Collected as part of a research study, without a referral diagnosis; a female subject 27 years old; a dermoscopic image of a skin lesion: 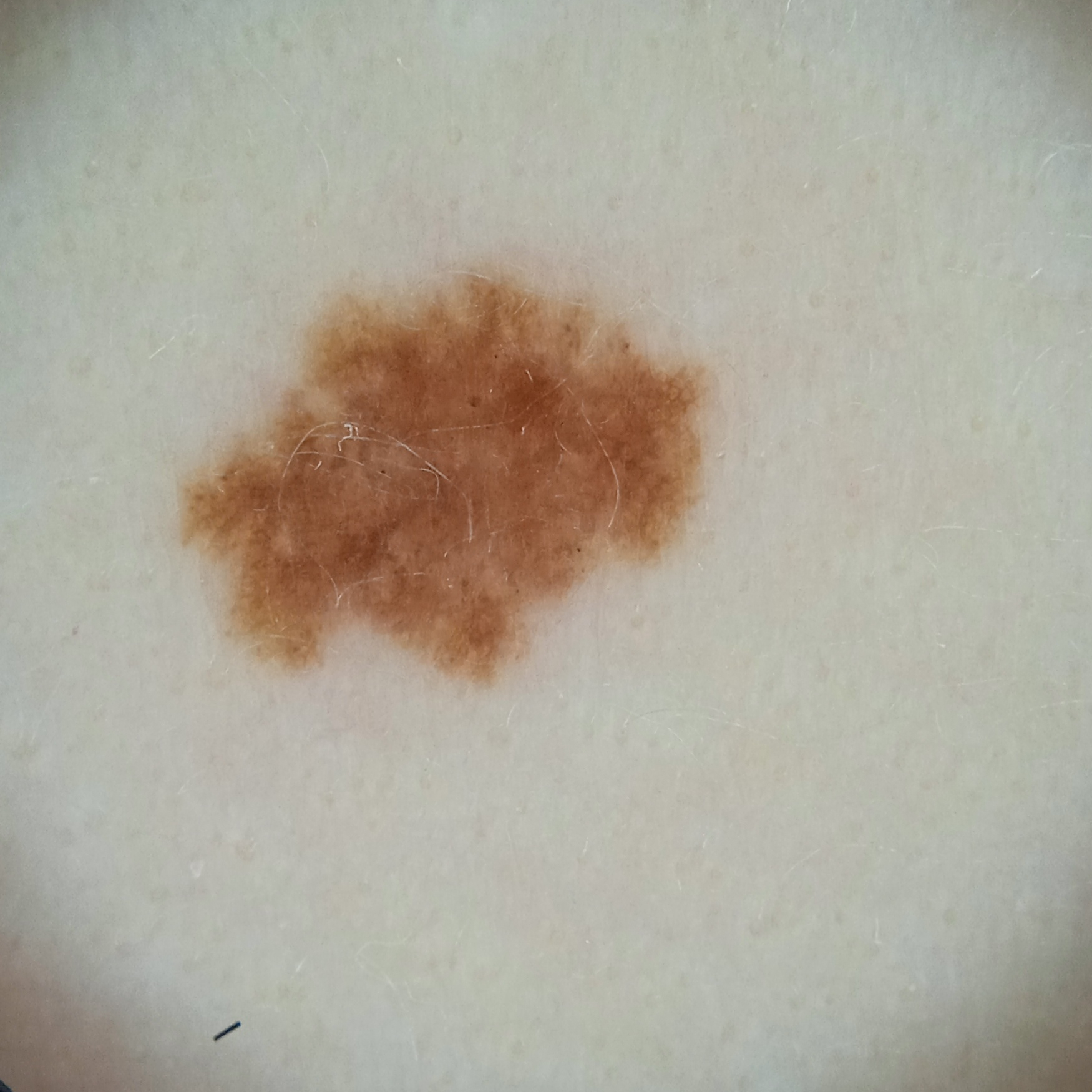Q: How large is the lesion?
A: 6.4 mm
Q: What was the diagnosis?
A: atypical (dysplastic) nevus — dermatologist consensus